Close-up view, the affected area is the palm.
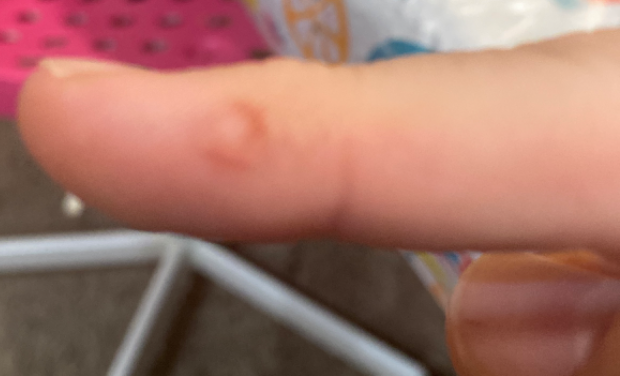The dermatologist could not determine a likely condition from the photograph alone.